A smartphone photograph of a skin lesion · FST II · a female subject 70 years of age · the chart records prior malignancy (patient or family): 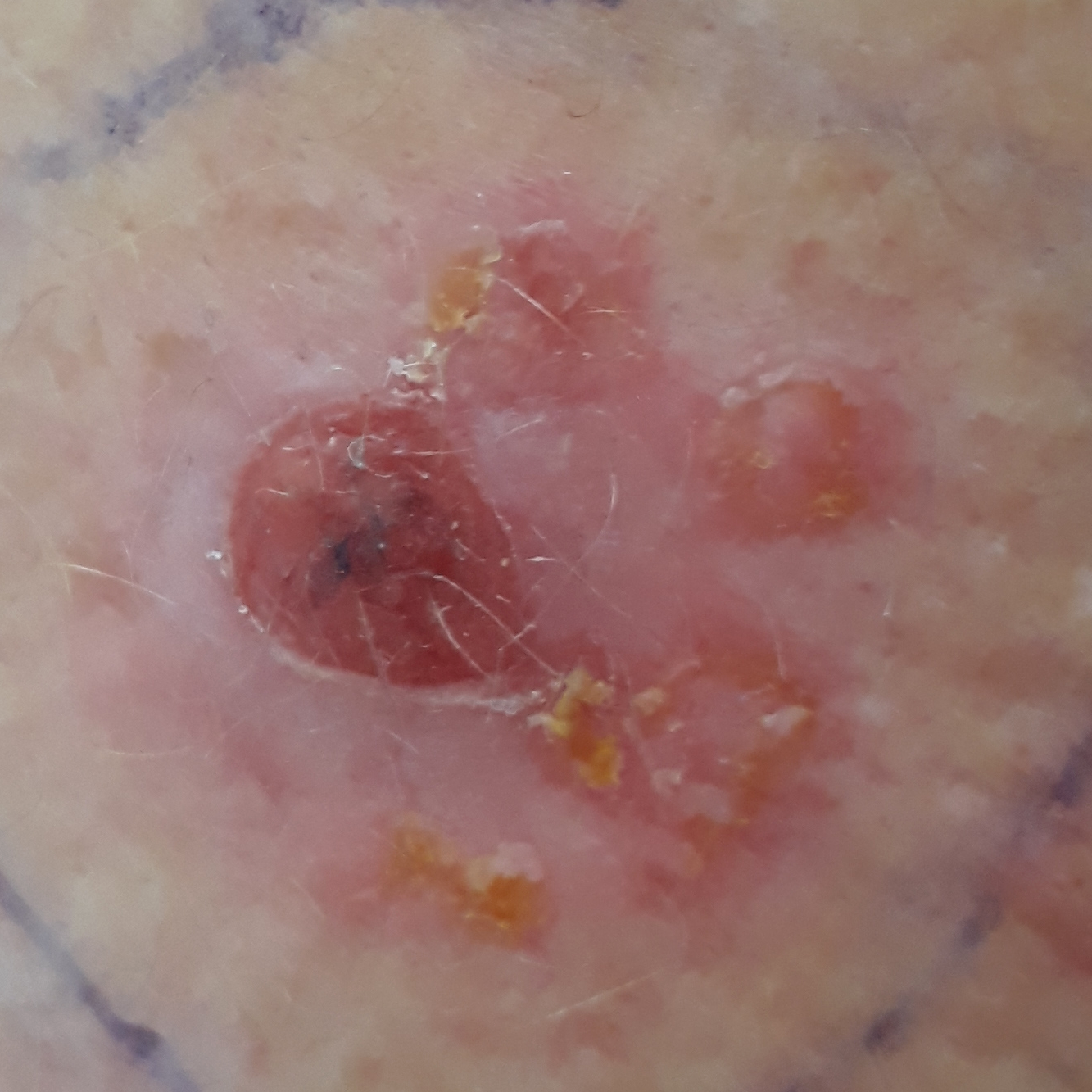| feature | finding |
|---|---|
| location | an arm |
| lesion size | 24 × 20 mm |
| reported symptoms | growth, bleeding, itching, pain |
| diagnostic label | squamous cell carcinoma (biopsy-proven) |